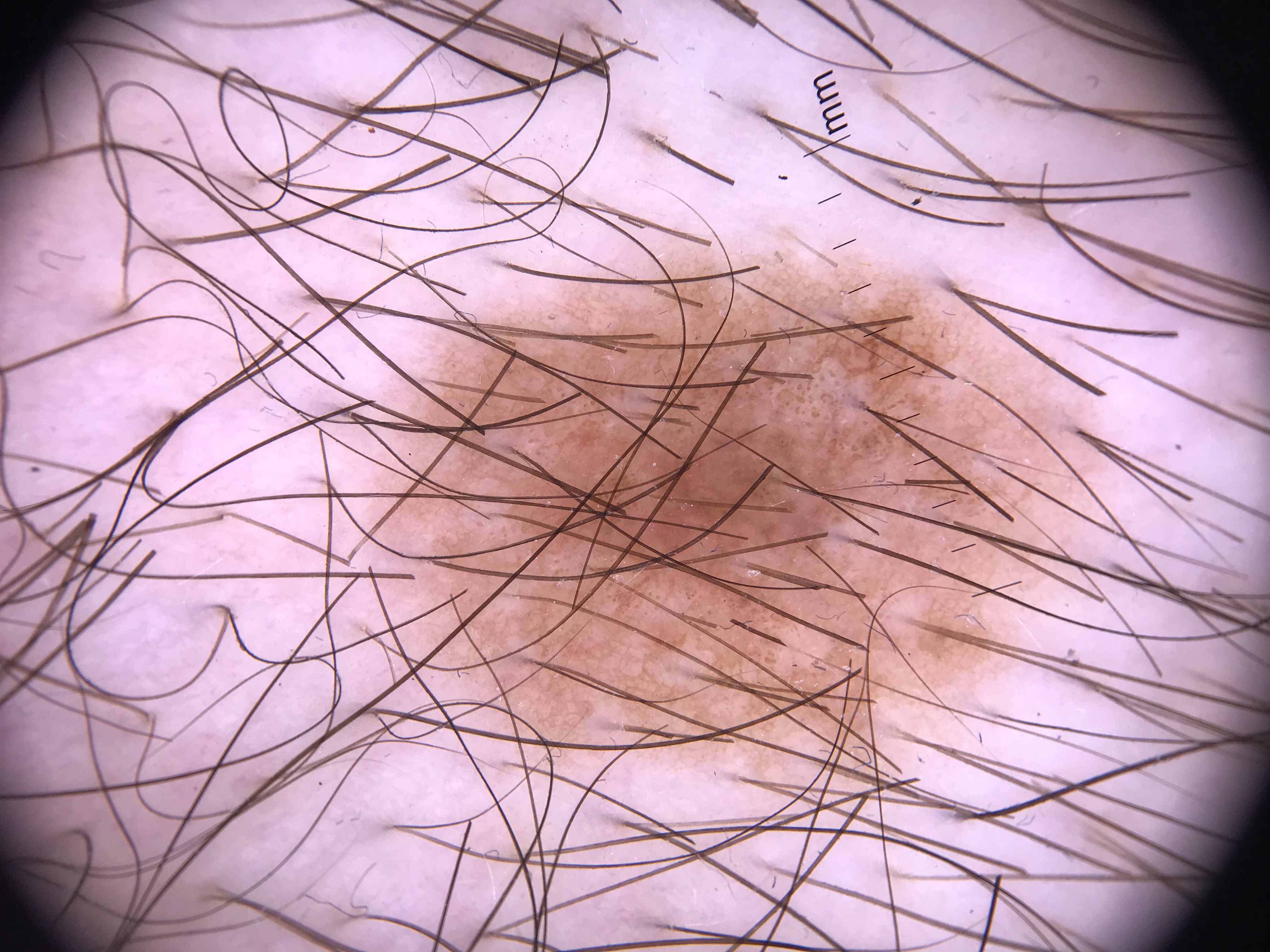- imaging: dermoscopy
- assessment: dysplastic junctional nevus (expert consensus)